The lesion involves the arm, leg, back of the torso and front of the torso. Self-categorized by the patient as acne. The photo was captured at an angle. Texture is reported as raised or bumpy. The subject is 18–29, male — 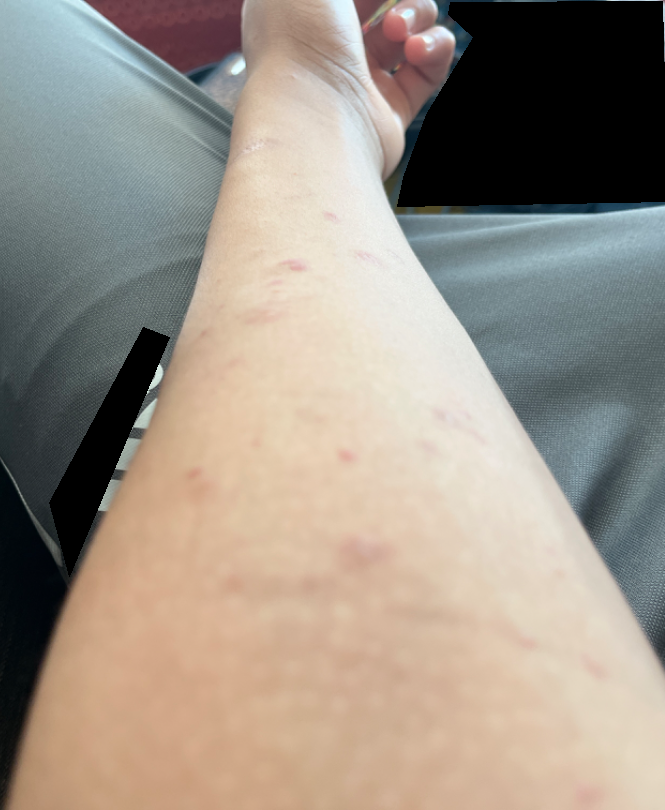Case summary:
* clinical impression: Insect Bite (39%); Allergic Contact Dermatitis (27%); Eczema (11%); Purpura (11%); Folliculitis (11%)